A dermoscopic photograph of a skin lesion: 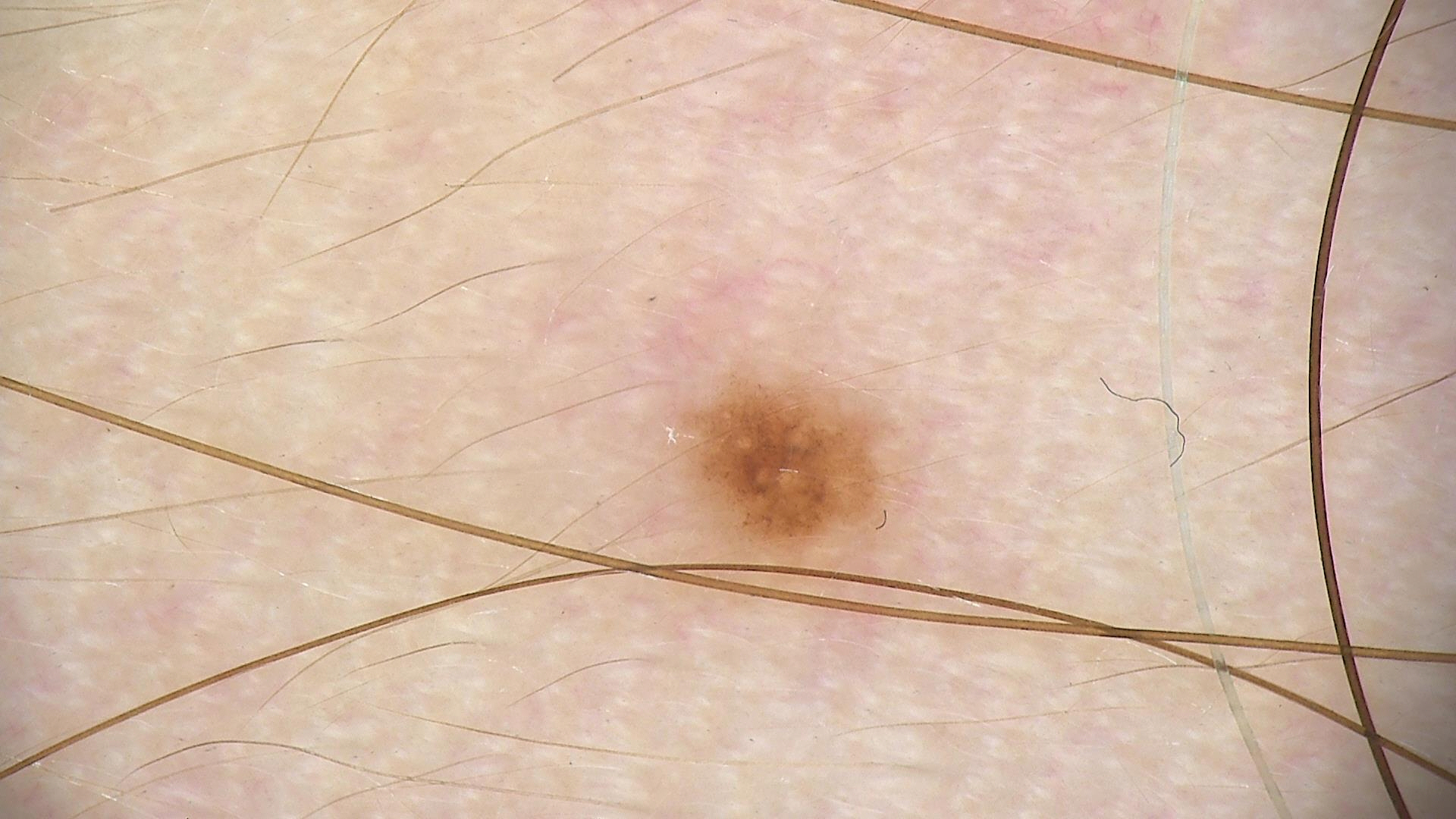{
  "diagnosis": {
    "name": "dysplastic junctional nevus",
    "code": "jd",
    "malignancy": "benign",
    "super_class": "melanocytic",
    "confirmation": "expert consensus"
  }
}